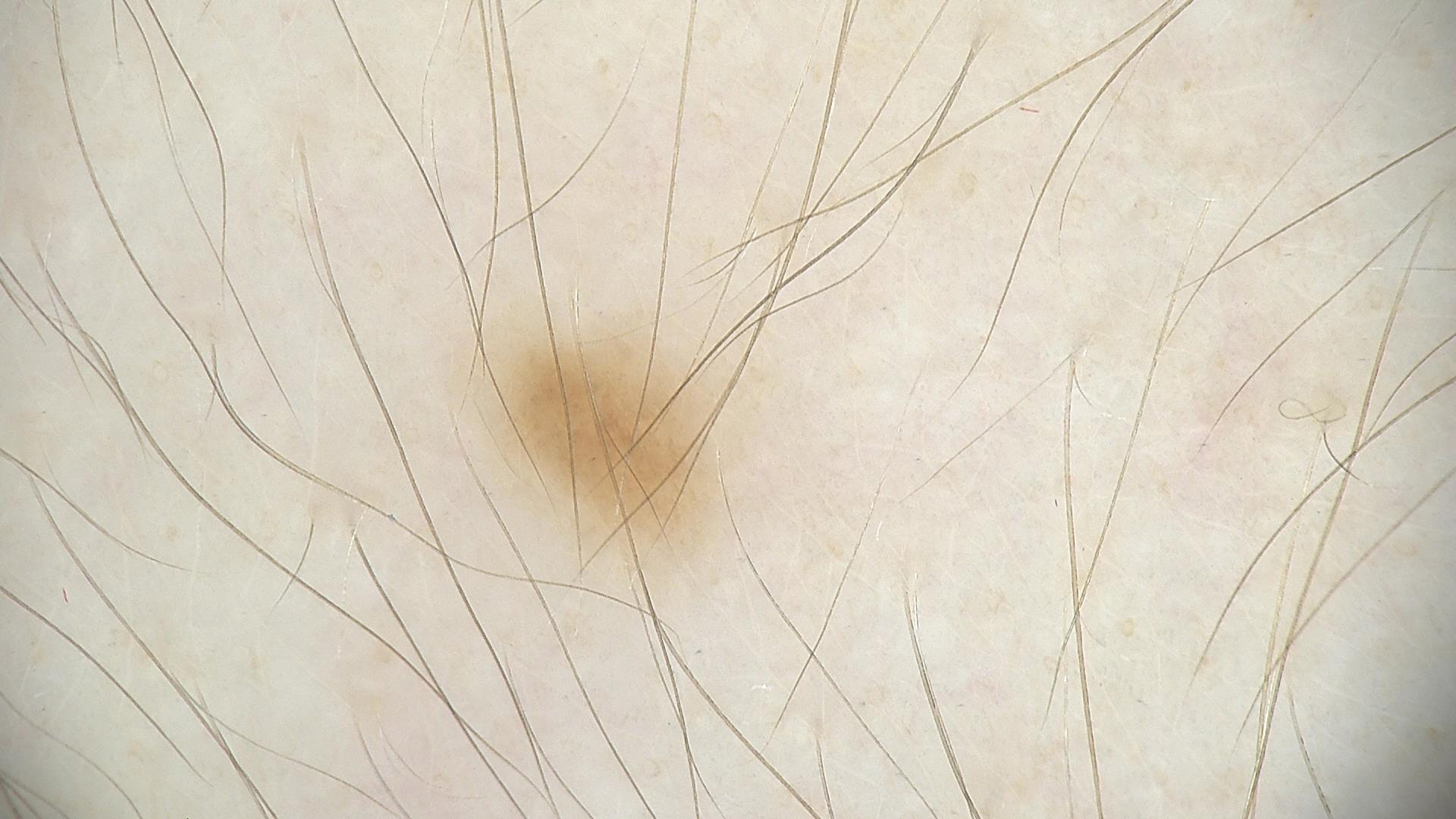{
  "diagnosis": {
    "name": "dysplastic junctional nevus",
    "code": "jd",
    "malignancy": "benign",
    "super_class": "melanocytic",
    "confirmation": "expert consensus"
  }
}